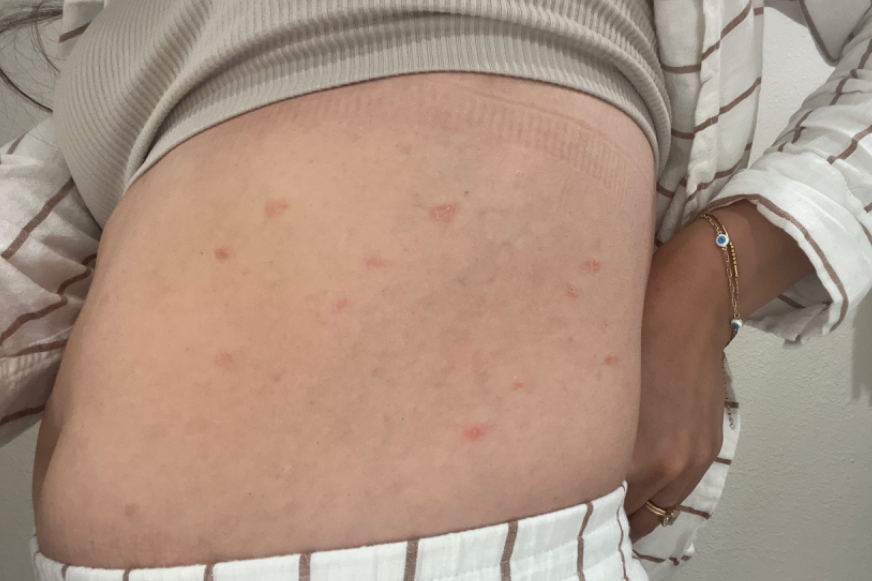Q: What was the assessment?
A: indeterminate
Q: Where on the body?
A: front of the torso, leg, arm and back of the torso
Q: What is the lesion texture?
A: rough or flaky and raised or bumpy
Q: Image view?
A: at a distance
Q: Reported symptoms?
A: none reported
Q: How long has this been present?
A: one to four weeks
Q: Patient's own categorization?
A: a rash